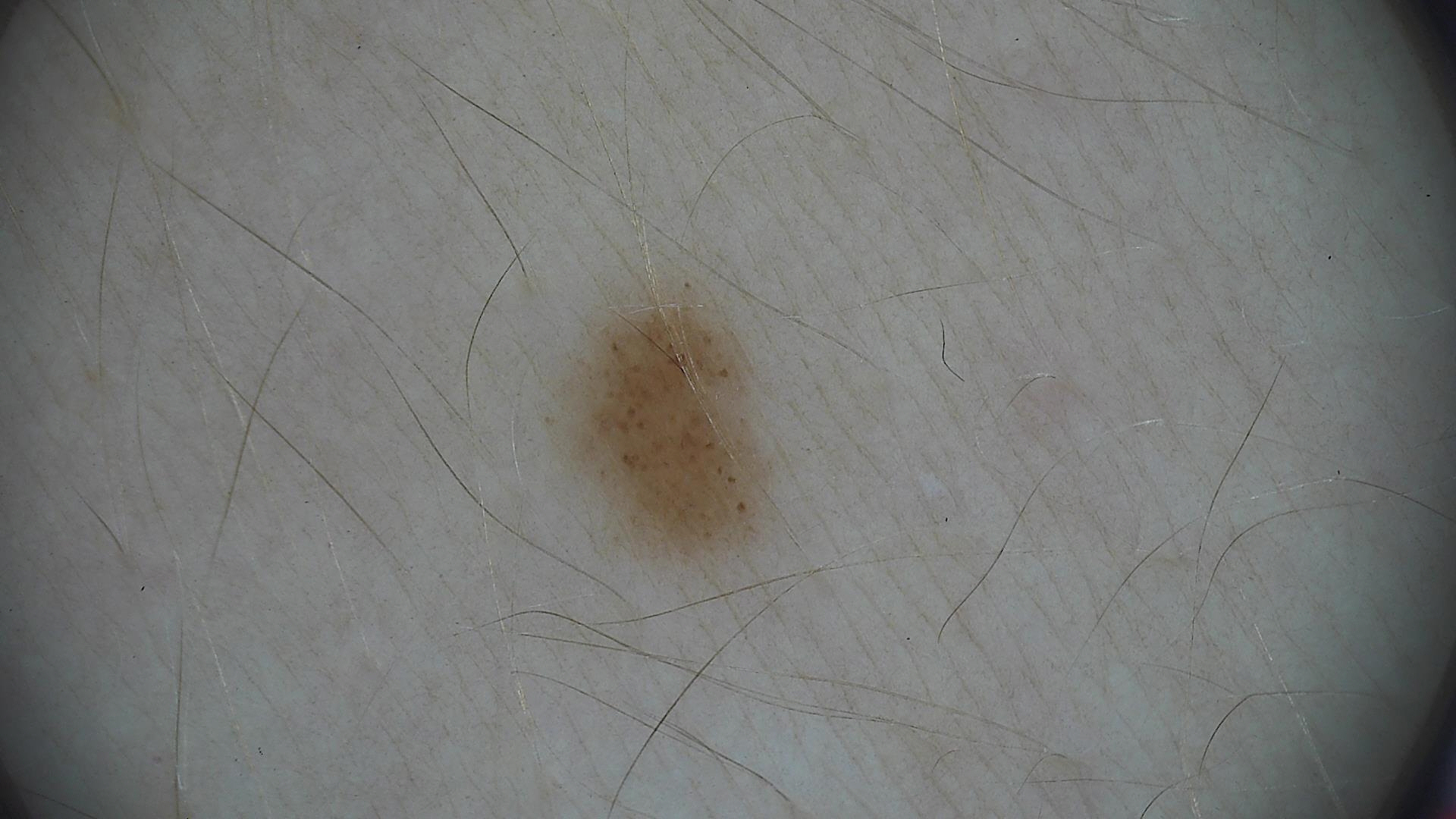A dermoscopic close-up of a skin lesion.
Consistent with an acral dysplastic junctional nevus.